Dermoscopy of a skin lesion.
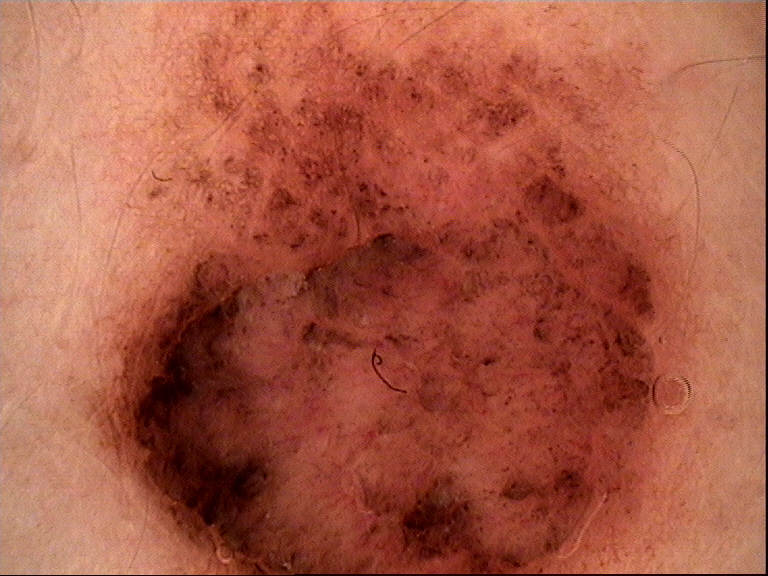The morphology is that of a banal lesion. Classified as a compound nevus.